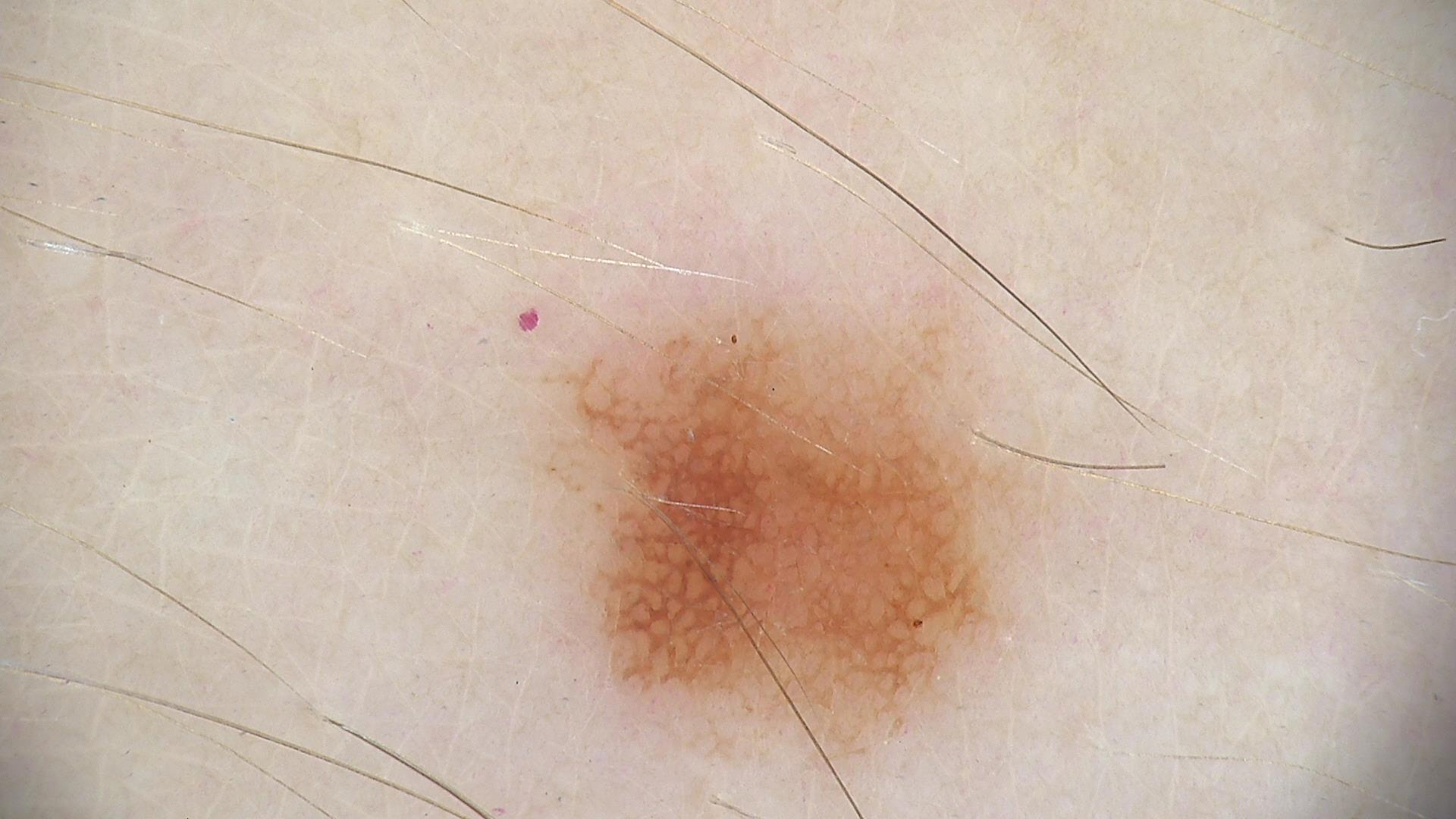assessment=dysplastic junctional nevus (expert consensus)